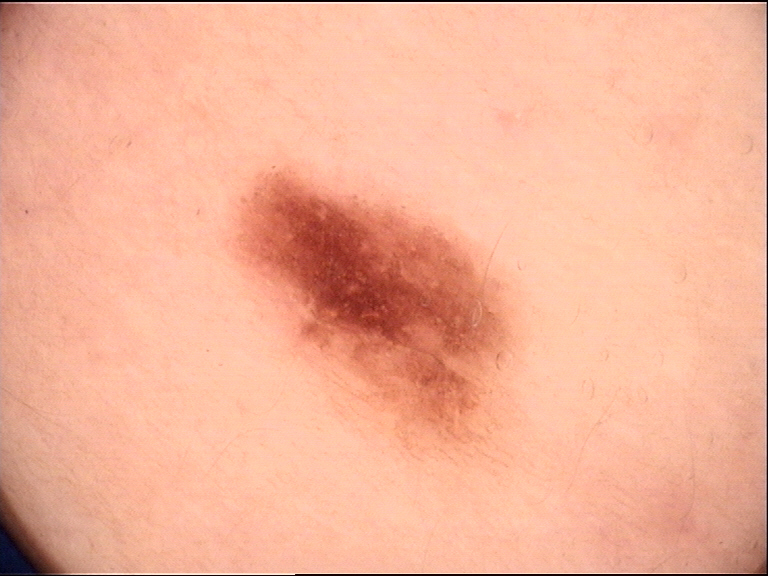A skin lesion imaged with a dermatoscope.
The diagnostic label was a benign lesion — a dysplastic junctional nevus.